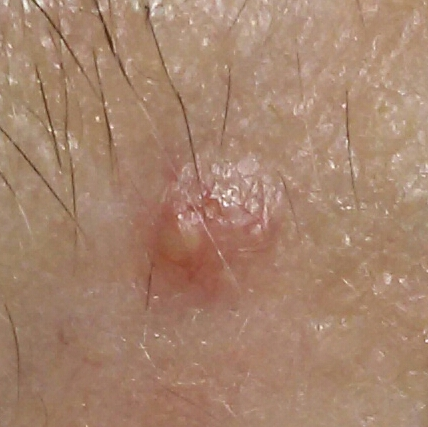diagnostic label: basal cell carcinoma (biopsy-proven).